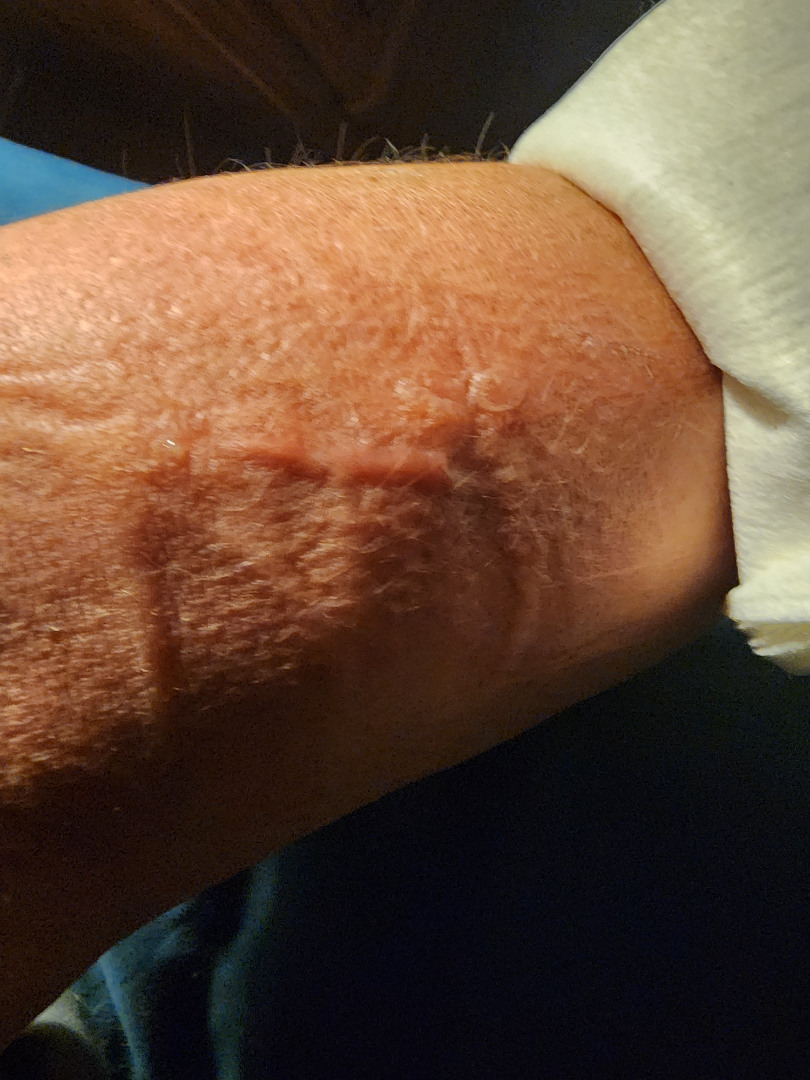assessment = not assessable; body site = arm; photo taken = close-up; contributor = female, age 40–49.